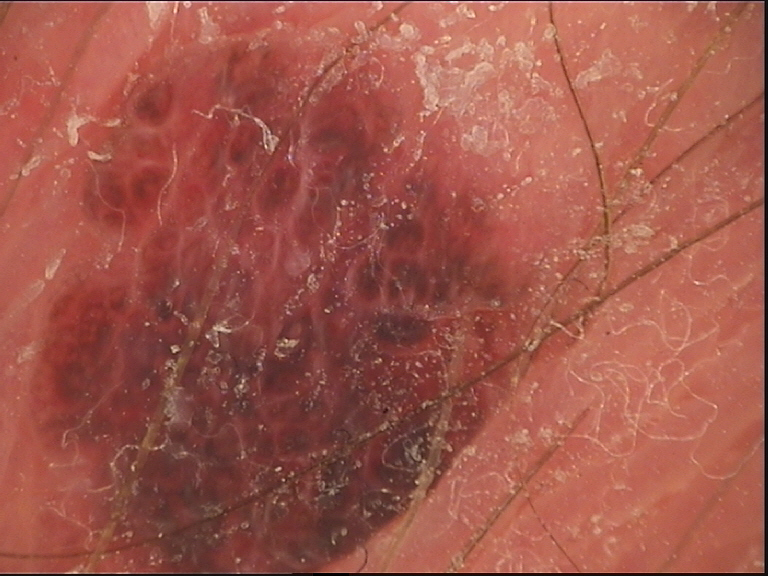Classified as a dermal nevus.